Close-up view, the back of the hand and arm are involved: 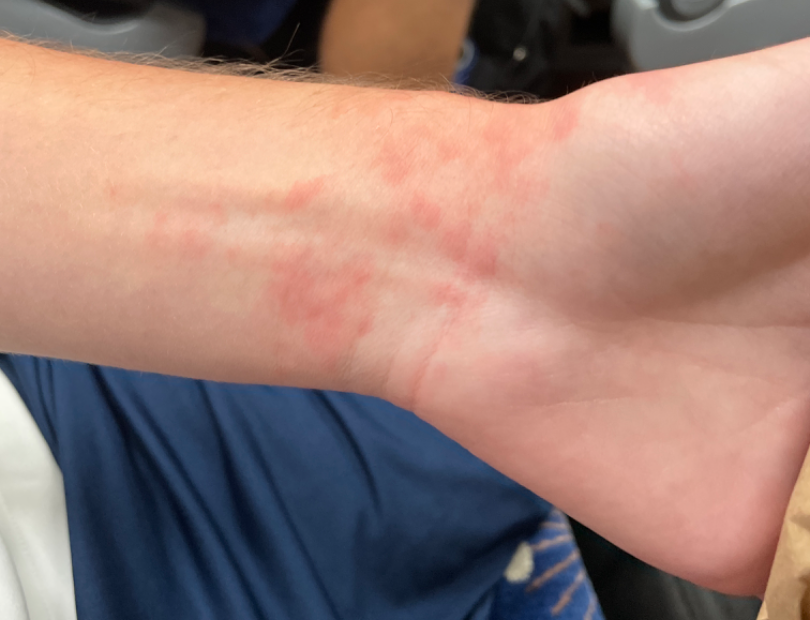Findings:
• lesion symptoms — itching
• surface texture — raised or bumpy
• self-categorized as — a rash
• diagnostic considerations — Eczema, Allergic Contact Dermatitis and Irritant Contact Dermatitis were considered with similar weight